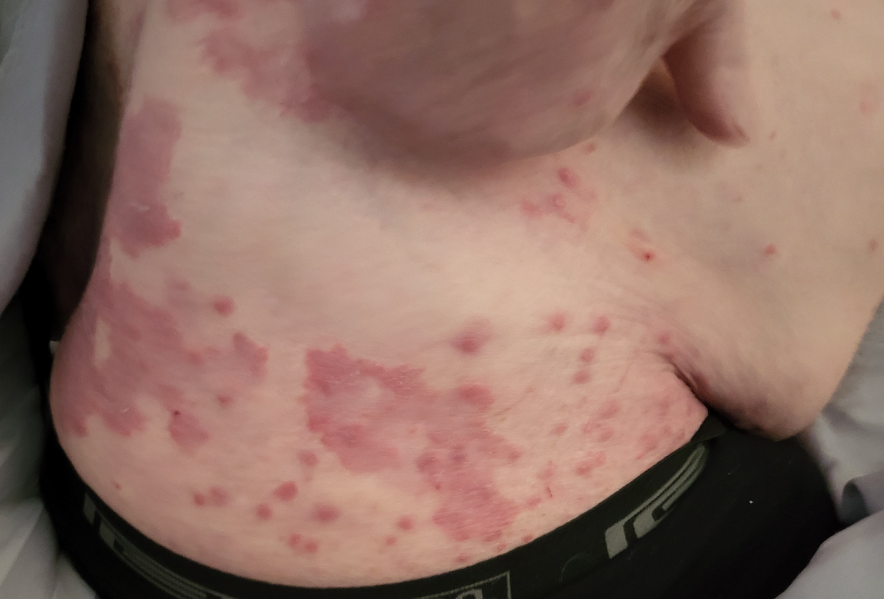Findings:
* assessment · not assessable
* framing · at an angle